Close-up view — 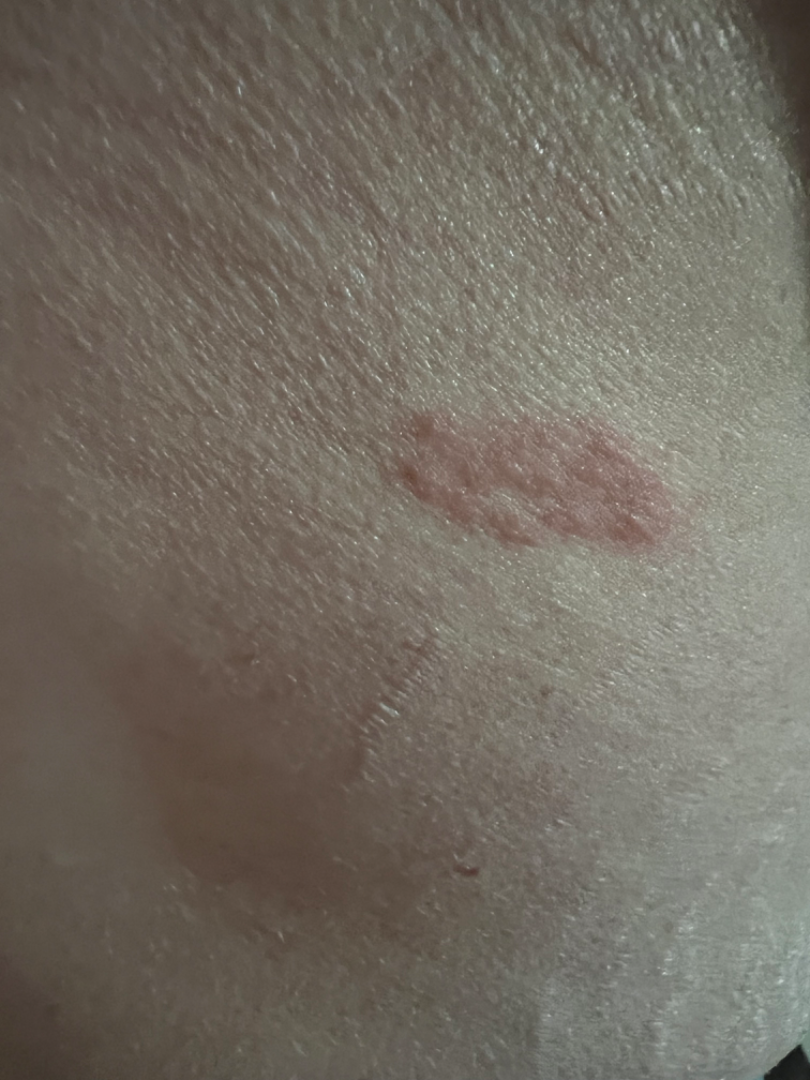Impression: On photographic review: the impression is Eczema.